A clinical photograph of a skin lesion; a subject in their 60s — 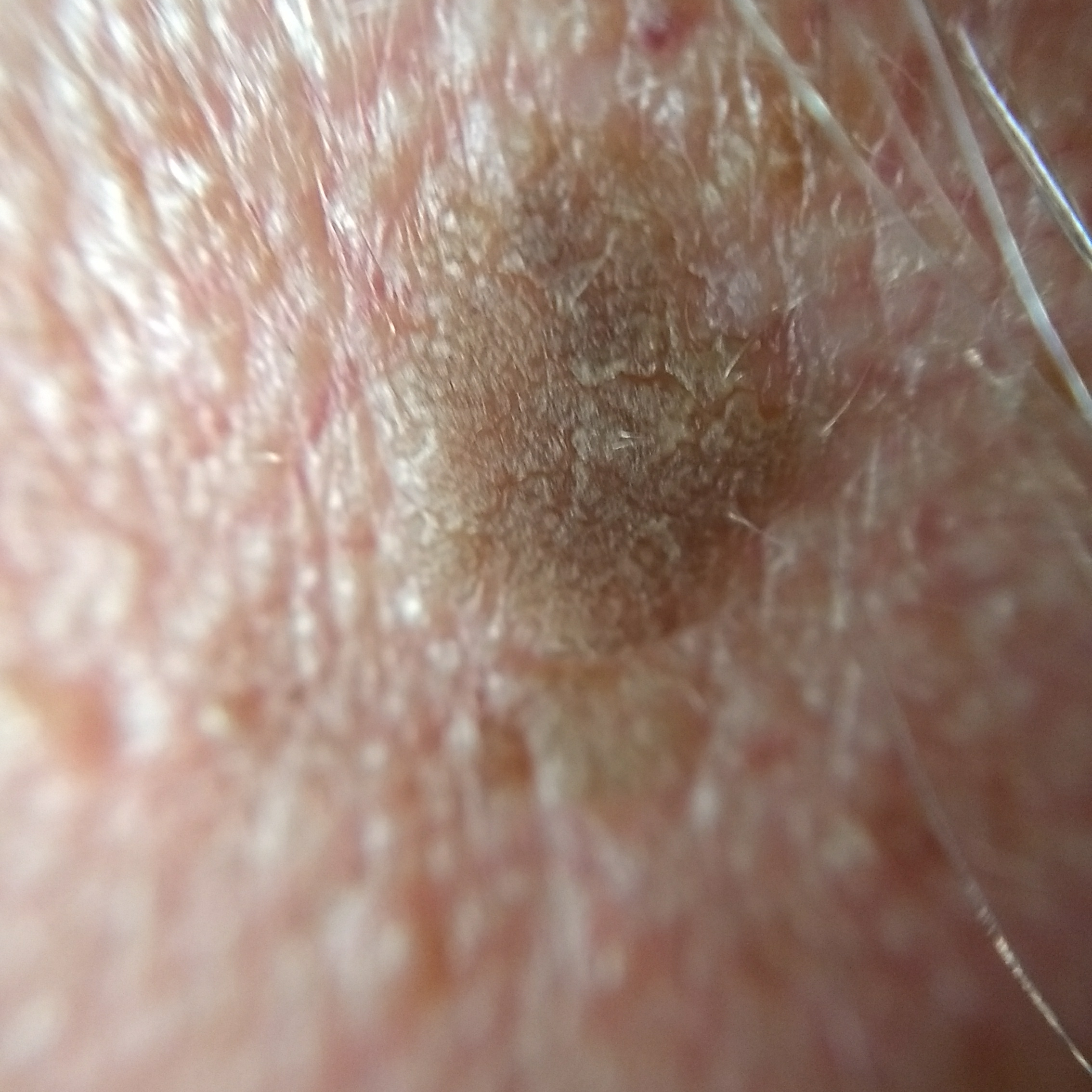Located on the face. The patient describes that the lesion is elevated, but does not hurt. Consistent with a seborrheic keratosis.